Dermoscopy of a skin lesion: 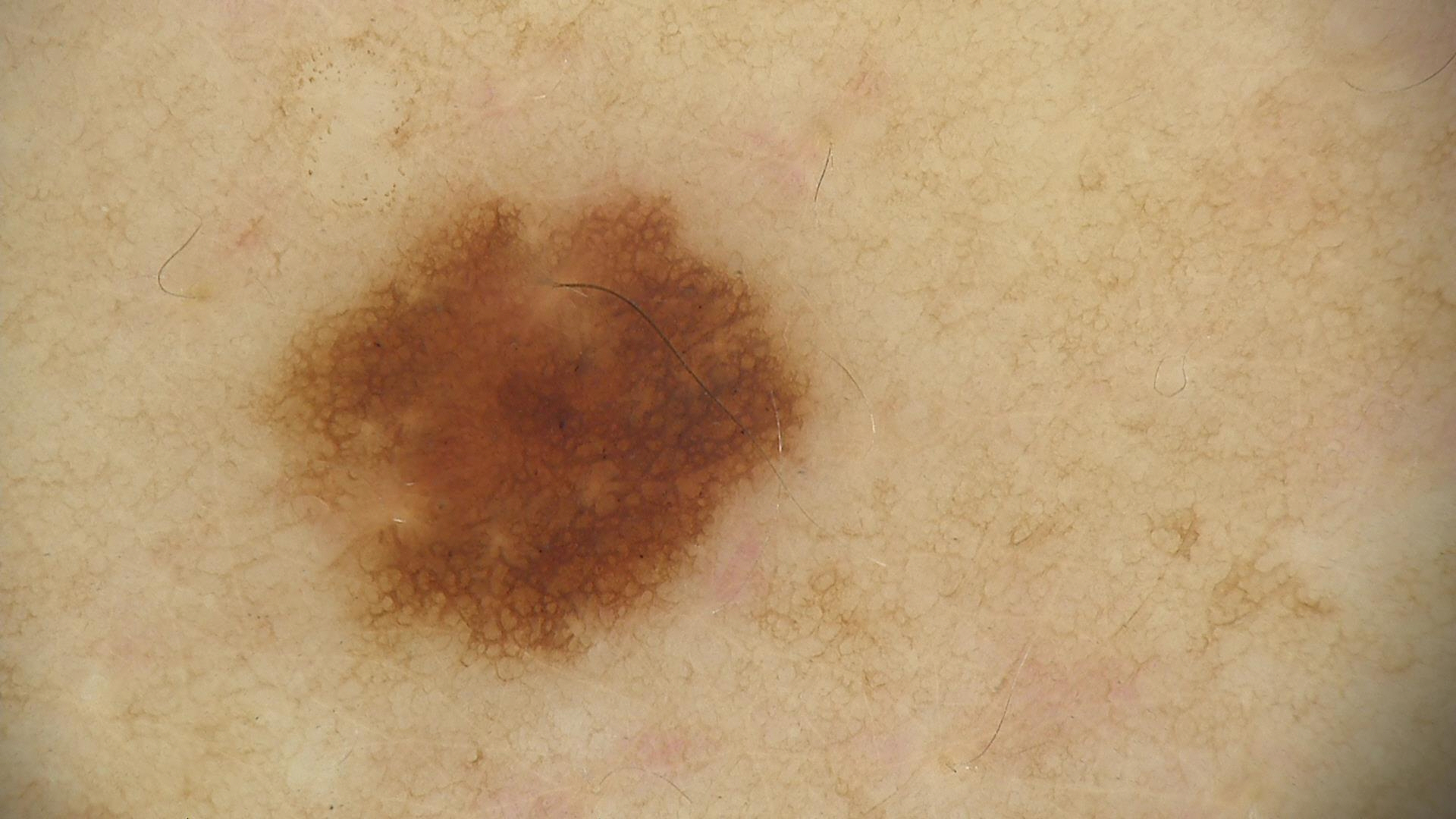* label: dysplastic junctional nevus (expert consensus)